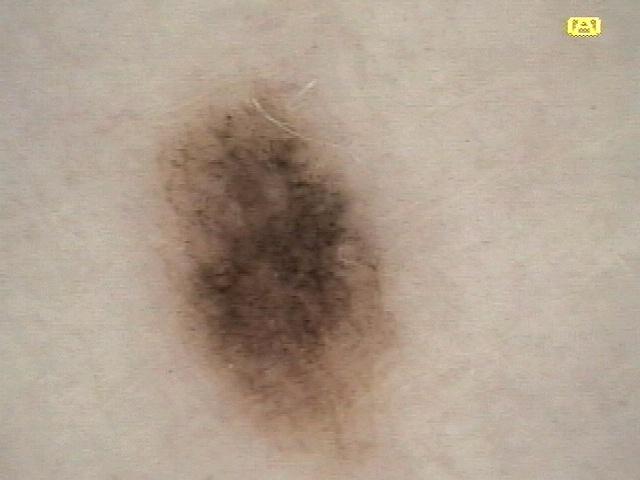skin_type: I
image: dermatoscopic image
patient:
  age_approx: 50
  sex: female
melanoma_history:
  personal_hx_melanoma: true
lesion_location:
  region: the trunk
  detail: the posterior trunk
diagnosis:
  name: Nevus
  malignancy: benign
  confirmation: expert clinical impression
  lineage: melanocytic